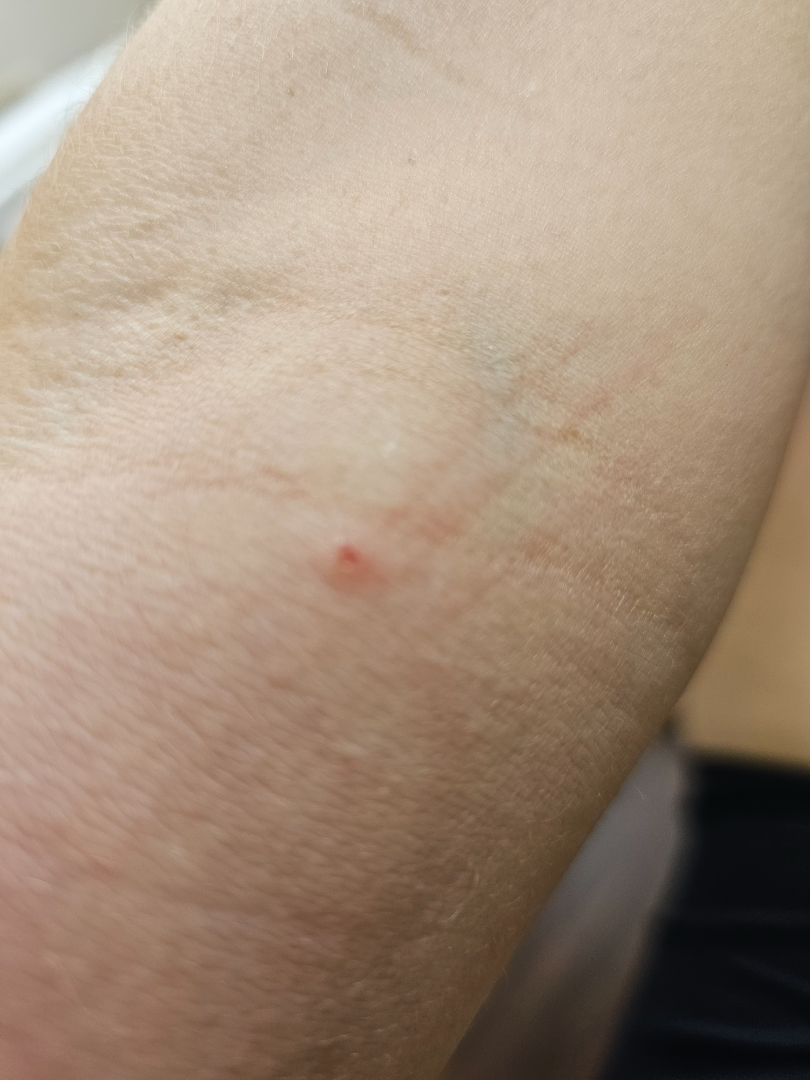| feature | finding |
|---|---|
| view | close-up |
| contributor | female, age 30–39 |
| site | head or neck, front of the torso, back of the torso and arm |
| differential | Insect Bite (54%); Eczema (23%); Urticaria (23%) |